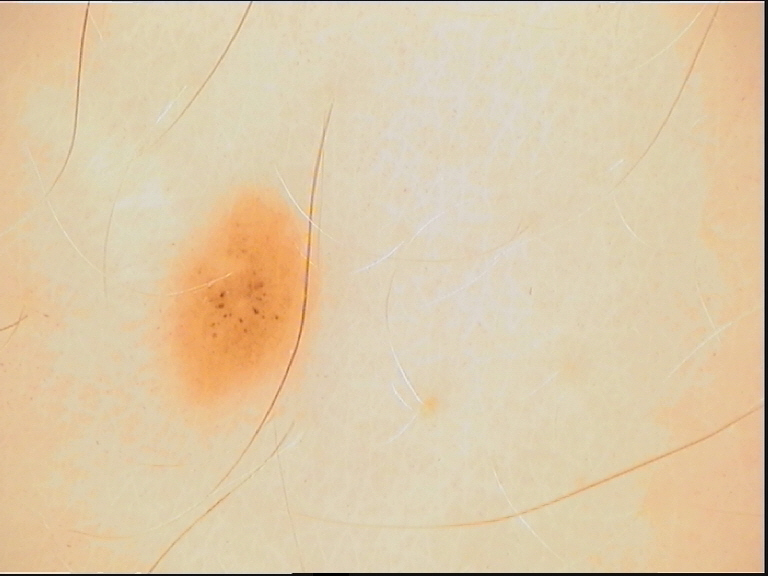The diagnosis was a dysplastic junctional nevus.